The photograph is a close-up of the affected area; the lesion involves the leg; the patient considered this a rash; female contributor, age 30–39; reported lesion symptoms include darkening and itching; the contributor reports the condition has been present for one to four weeks; the contributor reports the lesion is raised or bumpy: 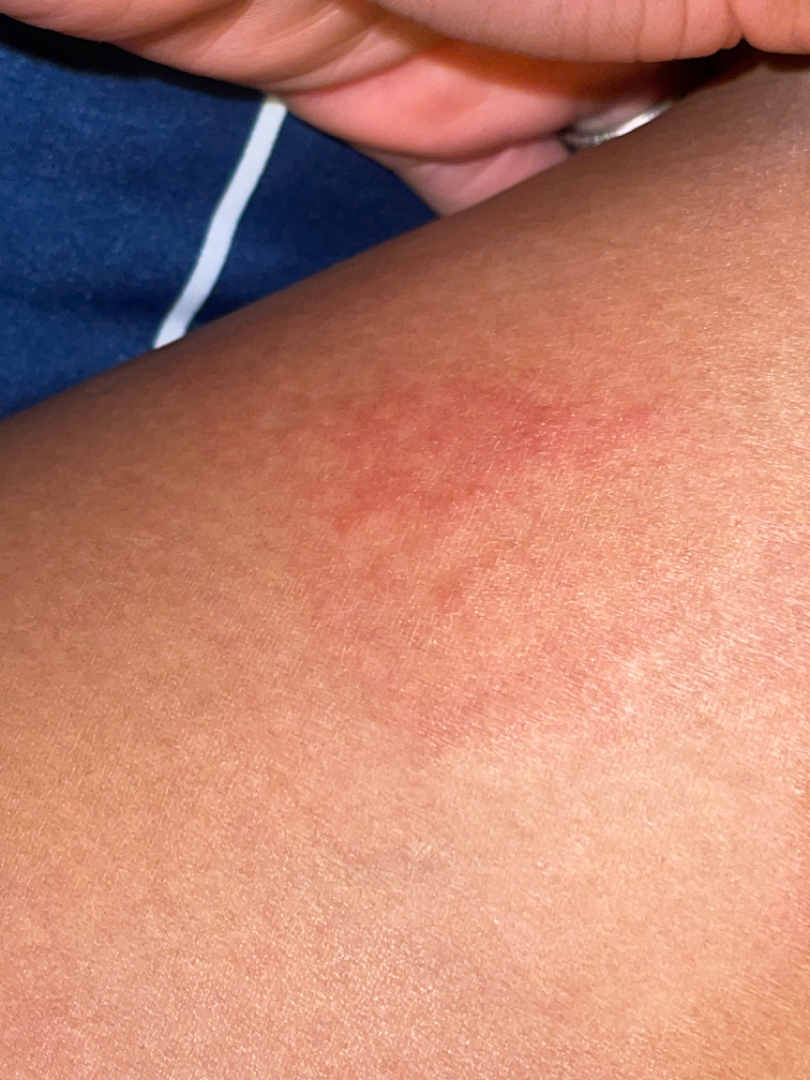| feature | finding |
|---|---|
| assessment | the leading consideration is Allergic Contact Dermatitis; possibly Eczema; also on the differential is Acute dermatitis, NOS; less likely is Urticaria; less probable is Tinea |